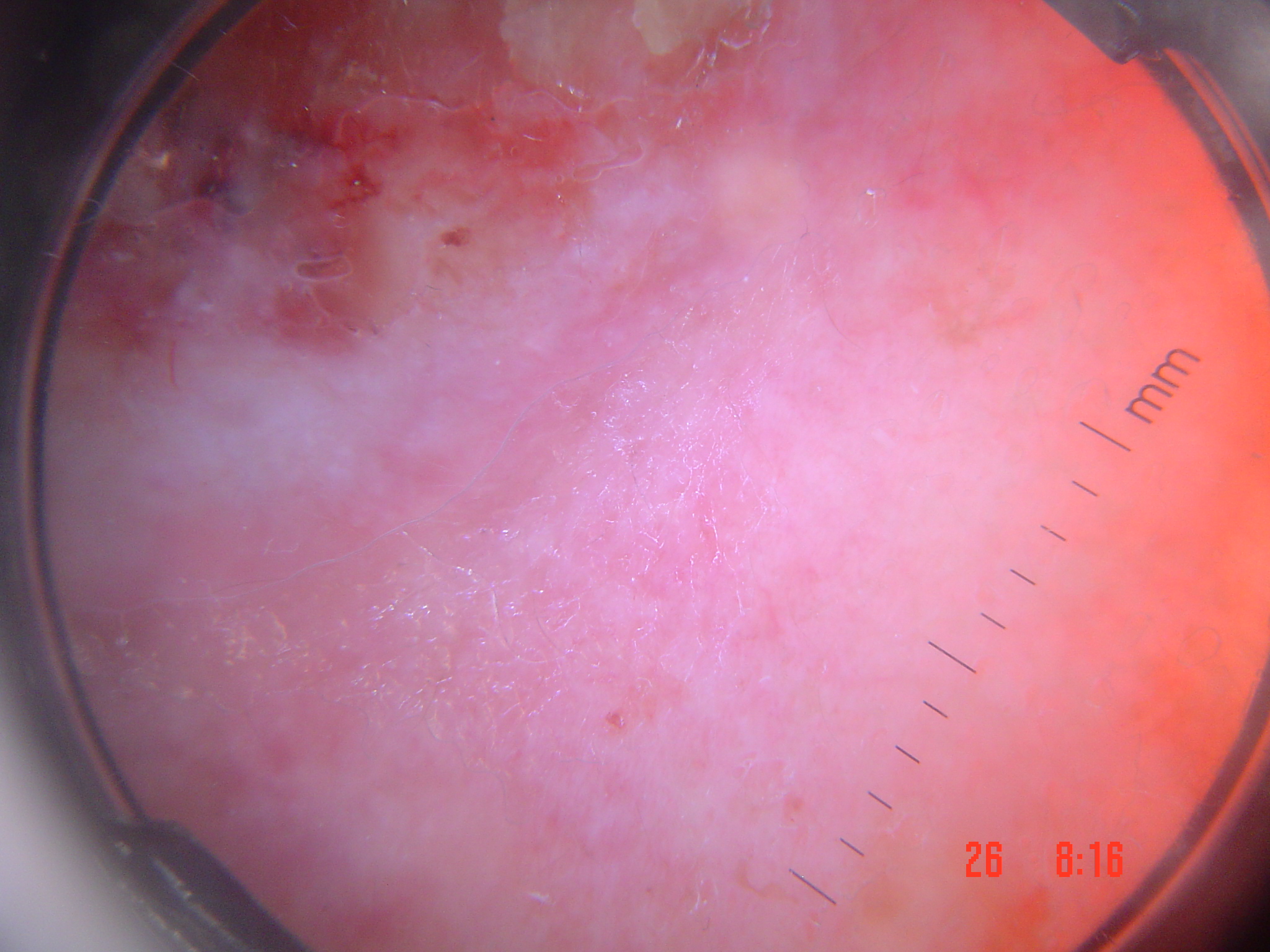A dermoscopic photograph of a skin lesion. Histopathologically confirmed as a malignant lesion — a squamous cell carcinoma.